The contributor is a female aged 18–29. The photograph was taken at an angle: 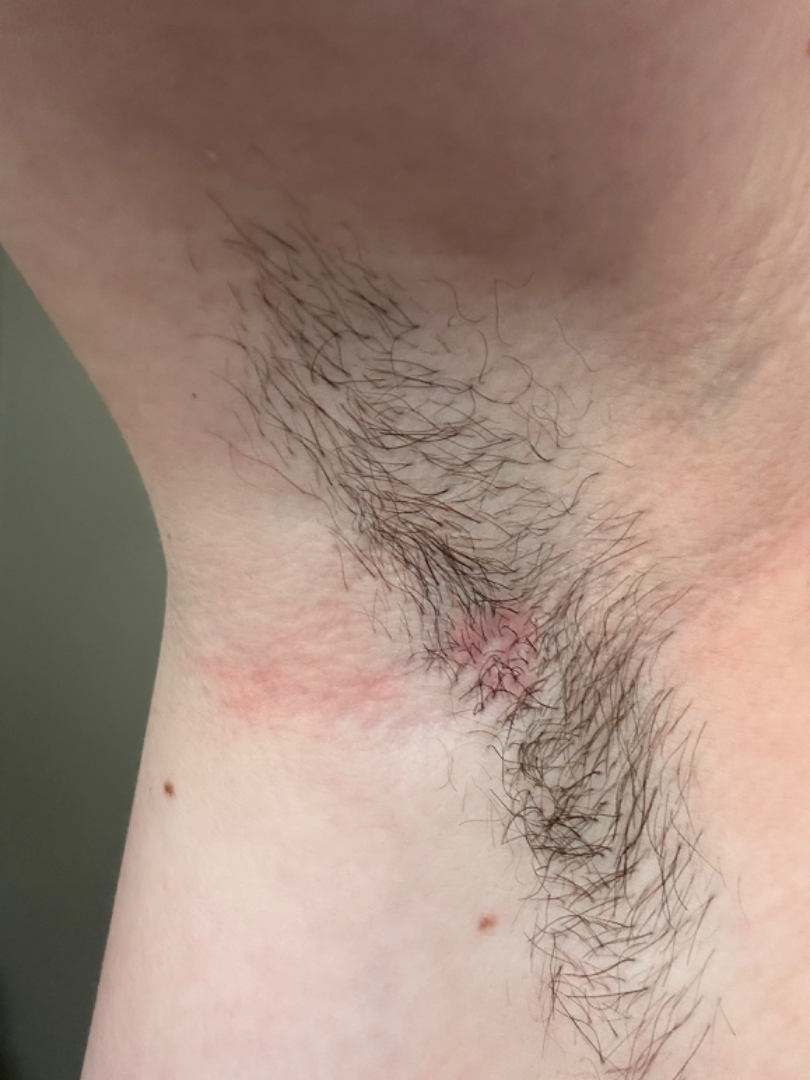The patient notes the condition has been present for three to twelve months. The lesion is associated with bothersome appearance. Texture is reported as flat. The impression was split between Intertrigo and Irritant Contact Dermatitis.